Symptoms reported: itching, the lesion involves the arm and back of the torso, the condition has been present for about one day, the patient notes the lesion is raised or bumpy, the photo was captured at an angle, the patient considered this a rash:
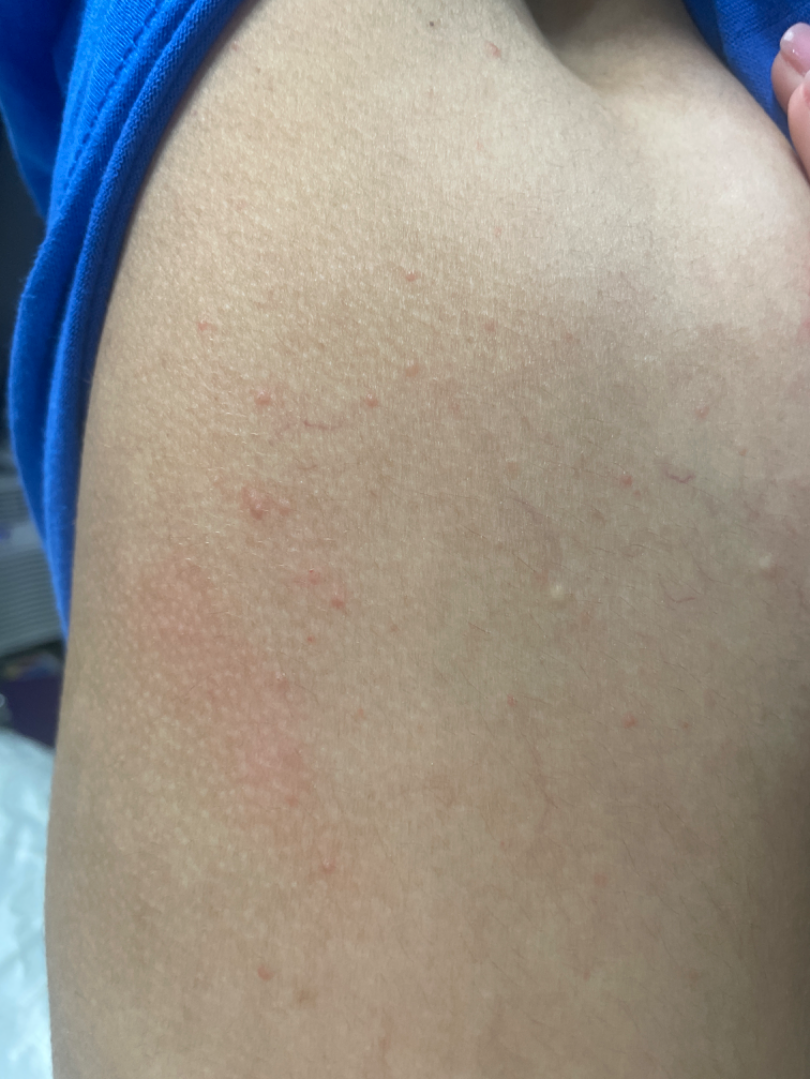Assessment:
The dermatologist could not determine a likely condition from the photograph alone.